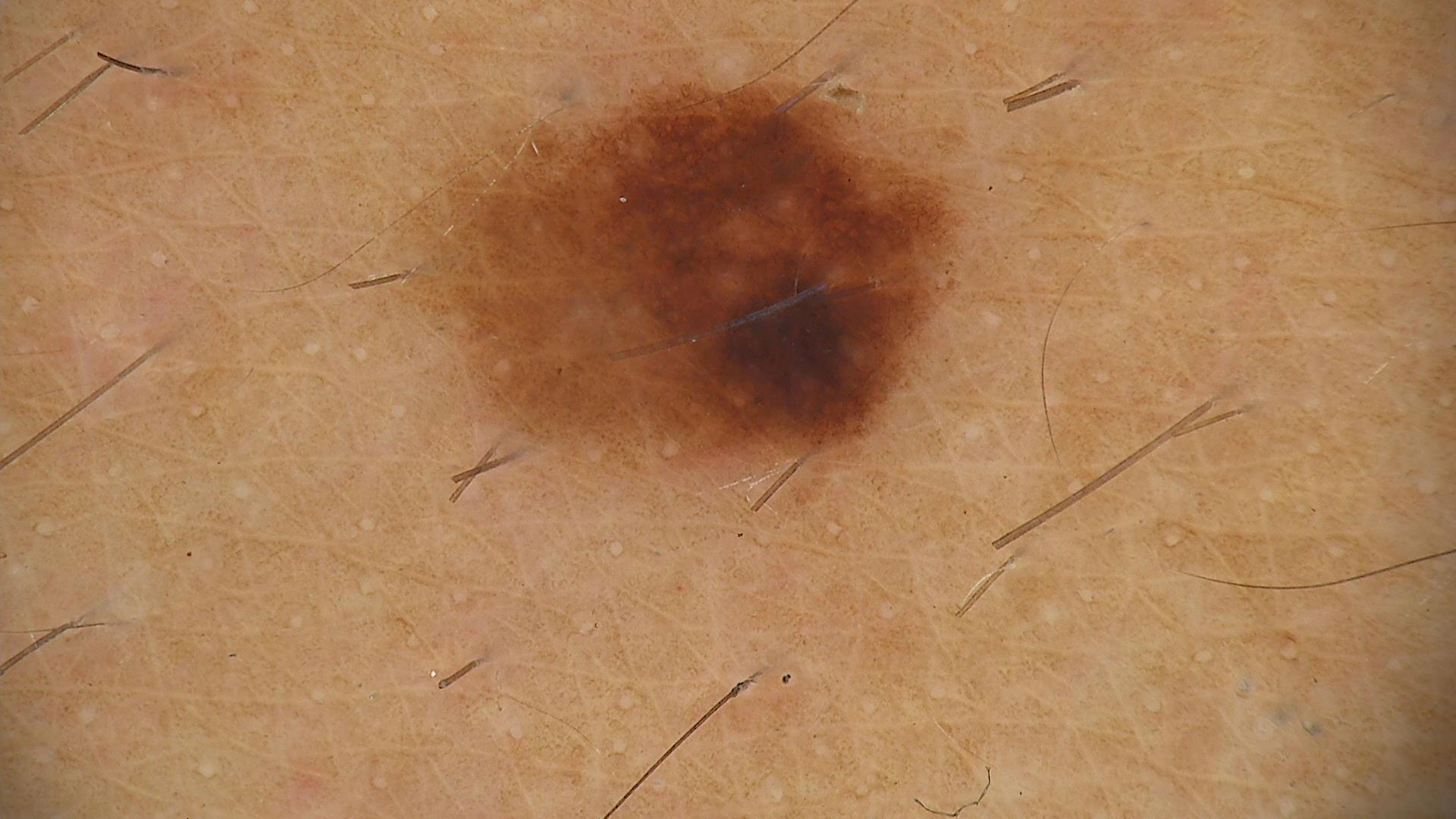{
  "image": "dermatoscopy",
  "diagnosis": {
    "name": "dysplastic junctional nevus",
    "code": "jd",
    "malignancy": "benign",
    "super_class": "melanocytic",
    "confirmation": "expert consensus"
  }
}